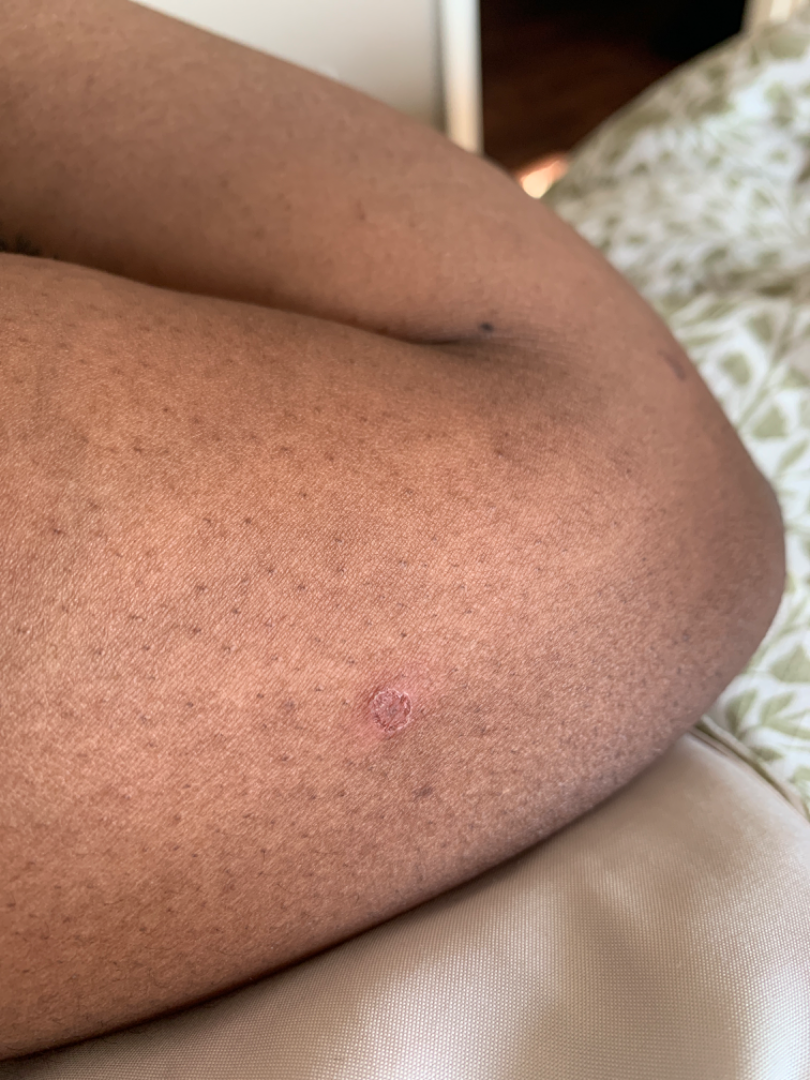The dermatologist could not determine a likely condition from the photograph alone. Close-up view. The patient described the issue as a rash. The arm is involved. Female contributor, age 18–29. Skin tone: Fitzpatrick V; human graders estimated MST 5 or 6 (two reviewer pools). Texture is reported as rough or flaky. Reported duration is less than one week.